Imaged for a research study, with no referral diagnosis recorded; the patient says their skin tans without first burning; a female subject age 92; a clinical close-up of a skin lesion; on a questionnaire the patient reported a personal history of cancer and a family history of skin cancer — 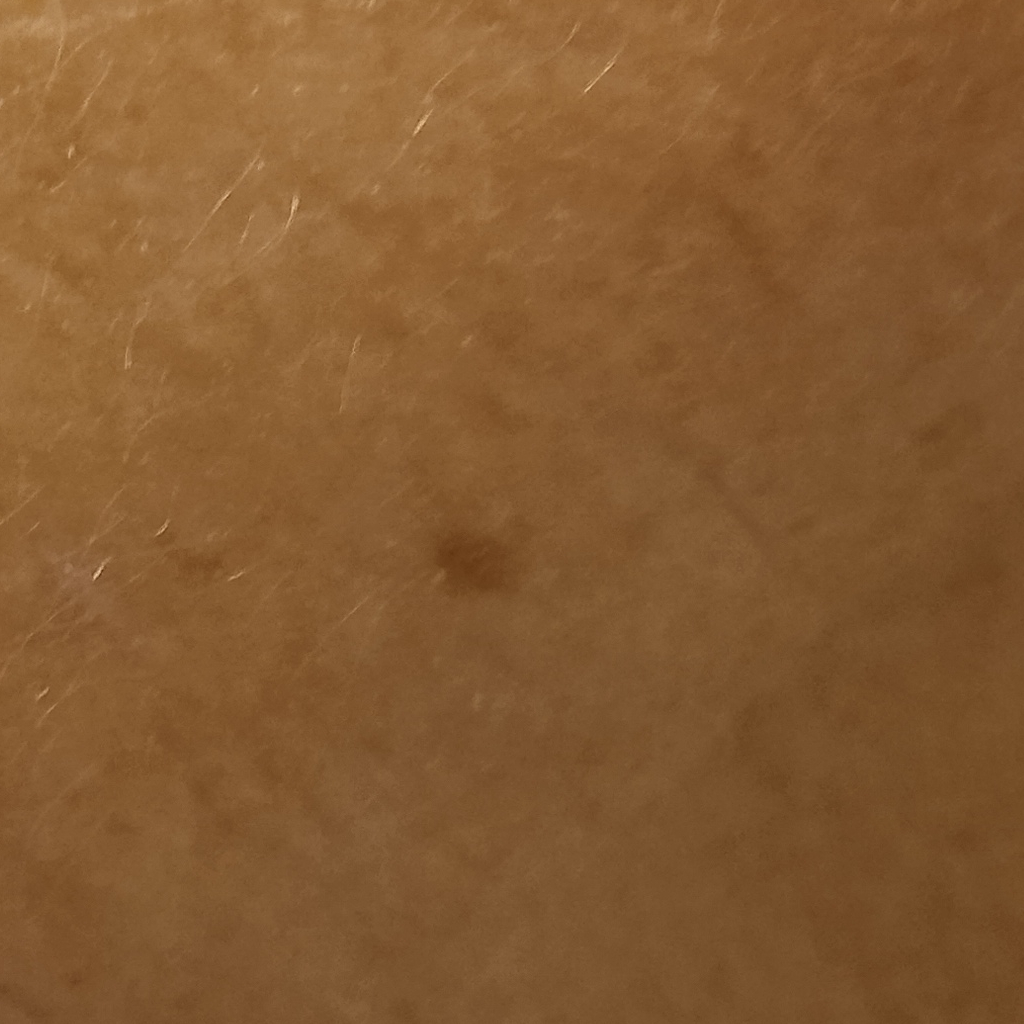body site=the face; size=2.9 mm; diagnosis=melanocytic nevus (dermatologist consensus).